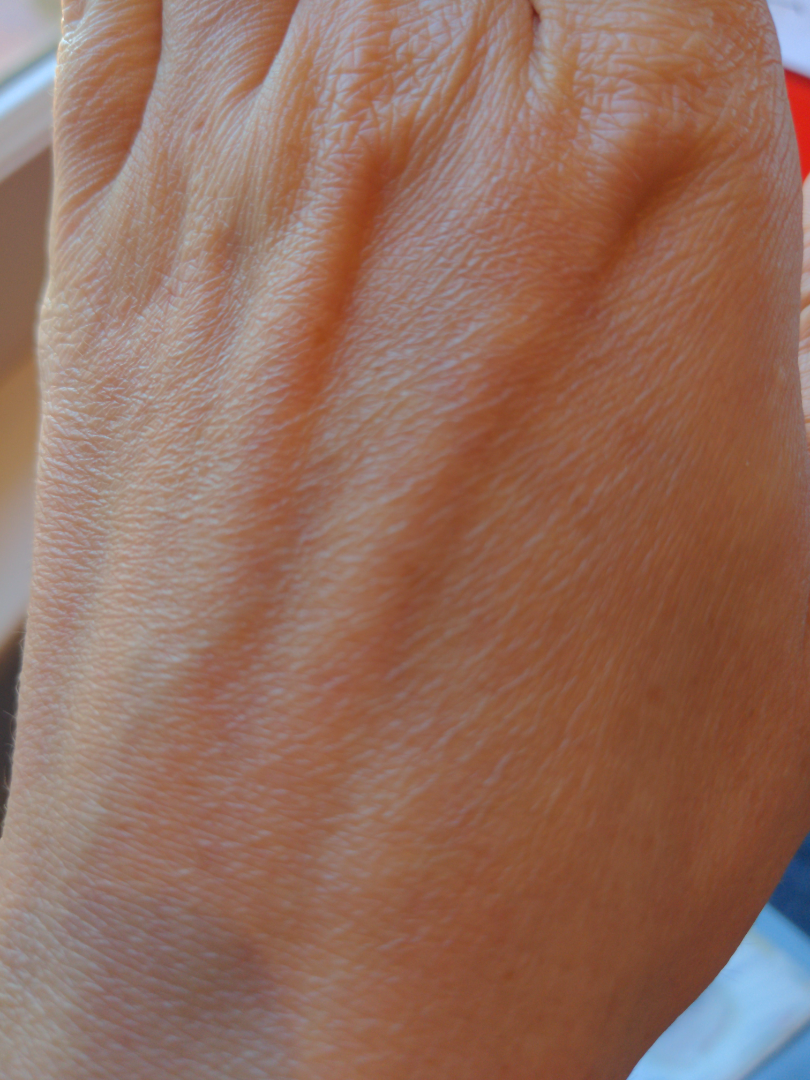- assessment: no skin condition identified
- skin tone: Fitzpatrick skin type I; non-clinician graders estimated 3 on the Monk skin tone scale
- framing: close-up